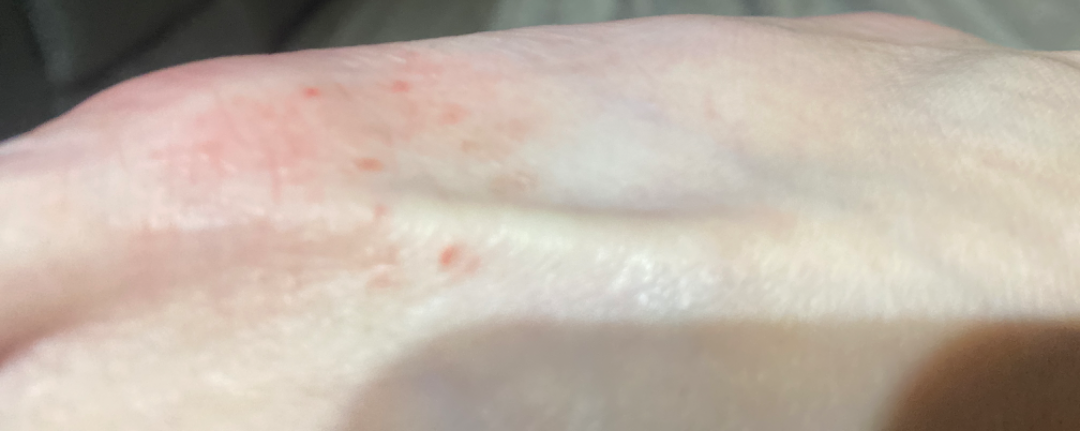differential:
  leading:
    - Eczema
  considered:
    - Tinea